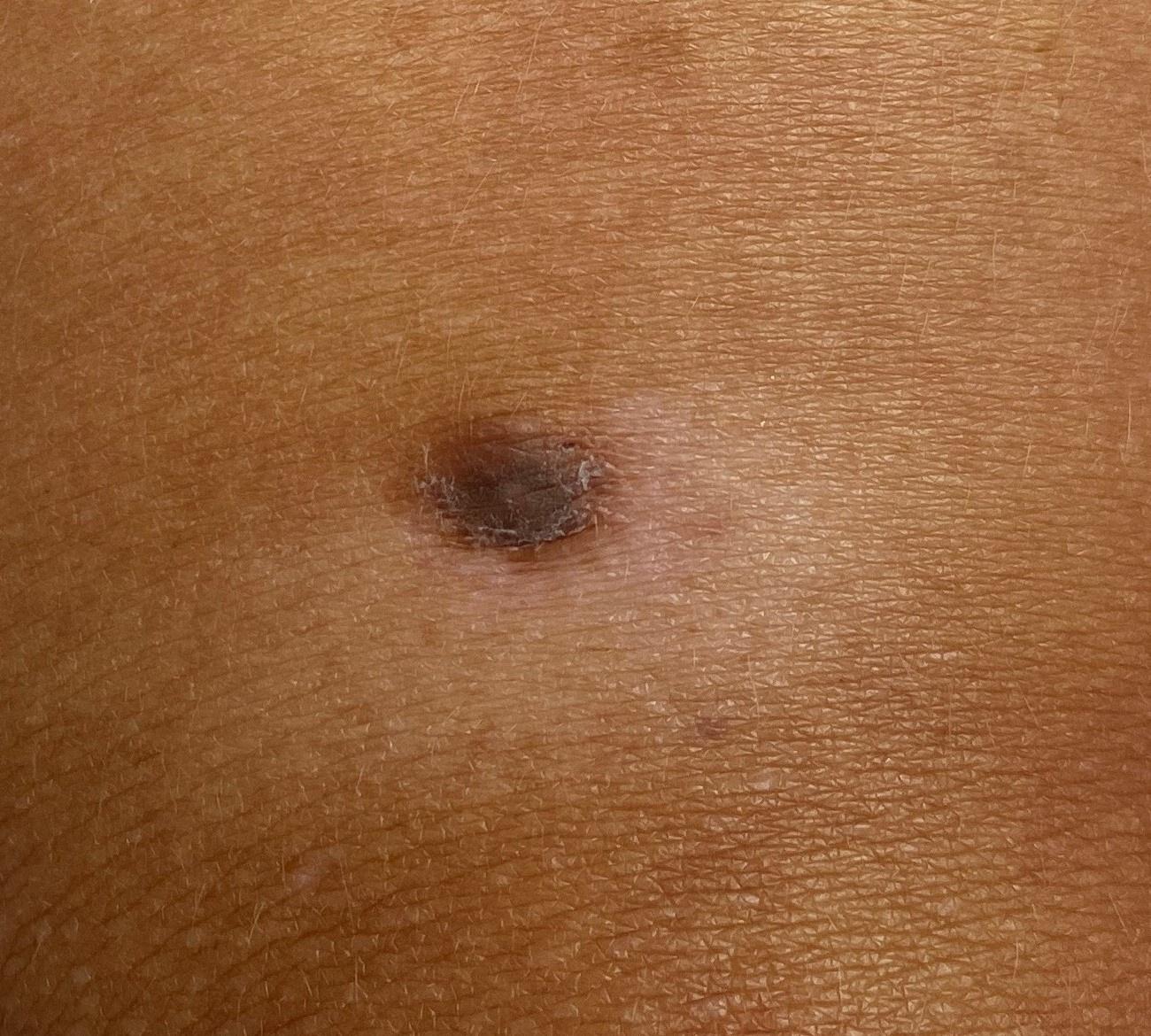Recorded as FST II. A female patient aged 38-42. A wide-field clinical photograph of a skin lesion. On biopsy, the diagnosis was a dermatofibroma.